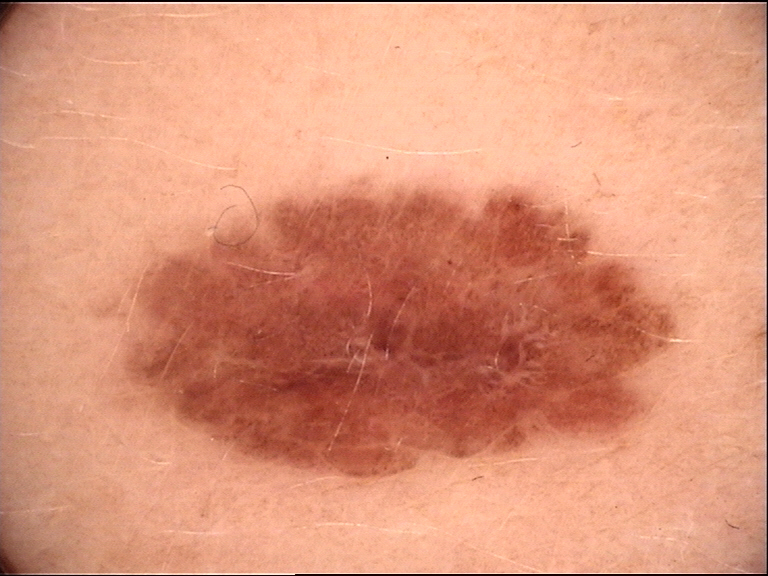Case: A dermoscopy image of a single skin lesion. Conclusion: Classified as a benign lesion — a dysplastic junctional nevus.